The photograph was taken at a distance: 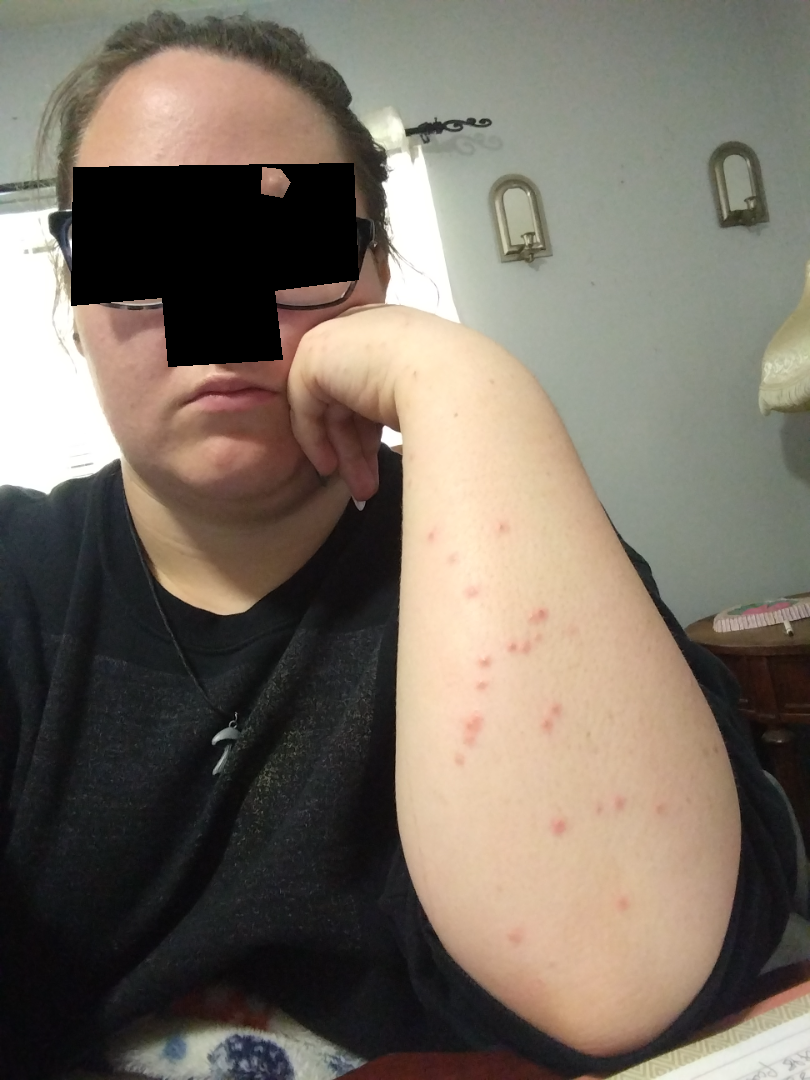clinical impression: the favored diagnosis is Insect Bite; possibly Eczema; an alternative is Molluscum Contagiosum